A skin lesion imaged with a dermatoscope — 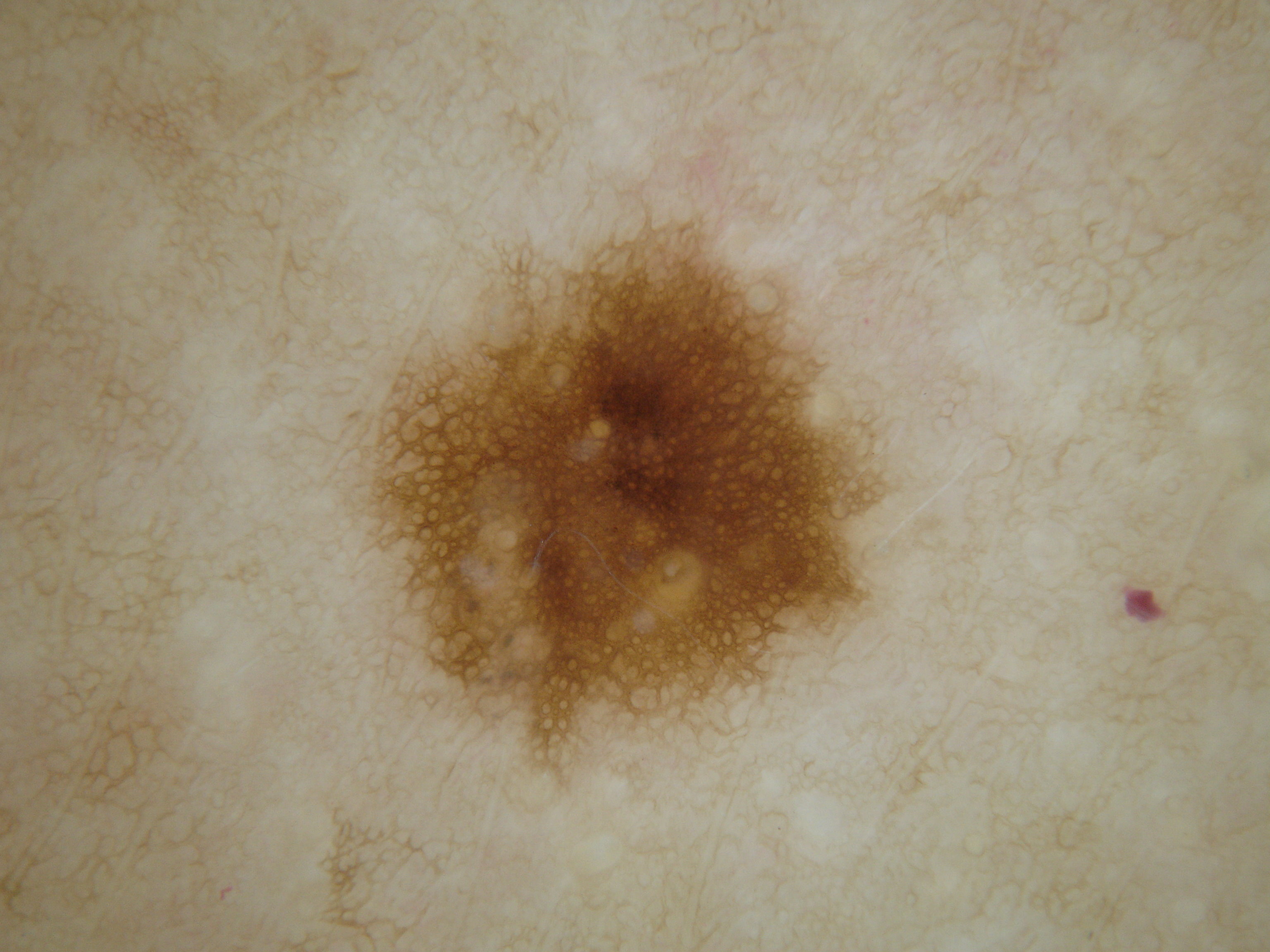| field | value |
|---|---|
| lesion location | [329,182,893,791] |
| features | pigment network |
| impression | a melanocytic nevus |